The head or neck and arm are involved. Close-up view. Female patient, age 40–49: 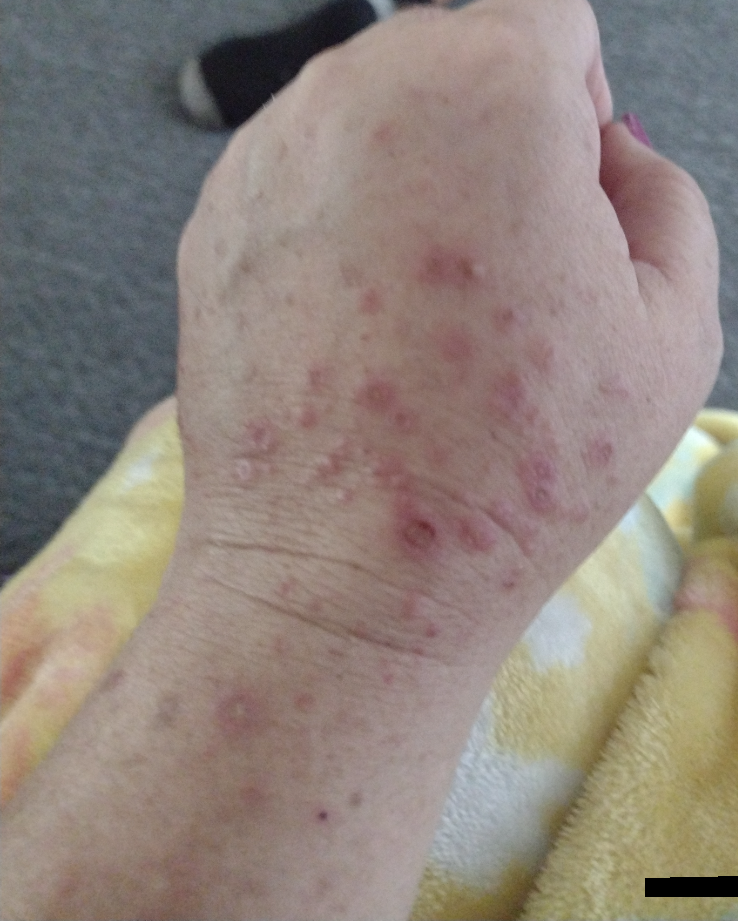<summary>
  <assessment>indeterminate</assessment>
  <texture>raised or bumpy, fluid-filled</texture>
  <symptoms>itching</symptoms>
  <duration>one to four weeks</duration>
</summary>